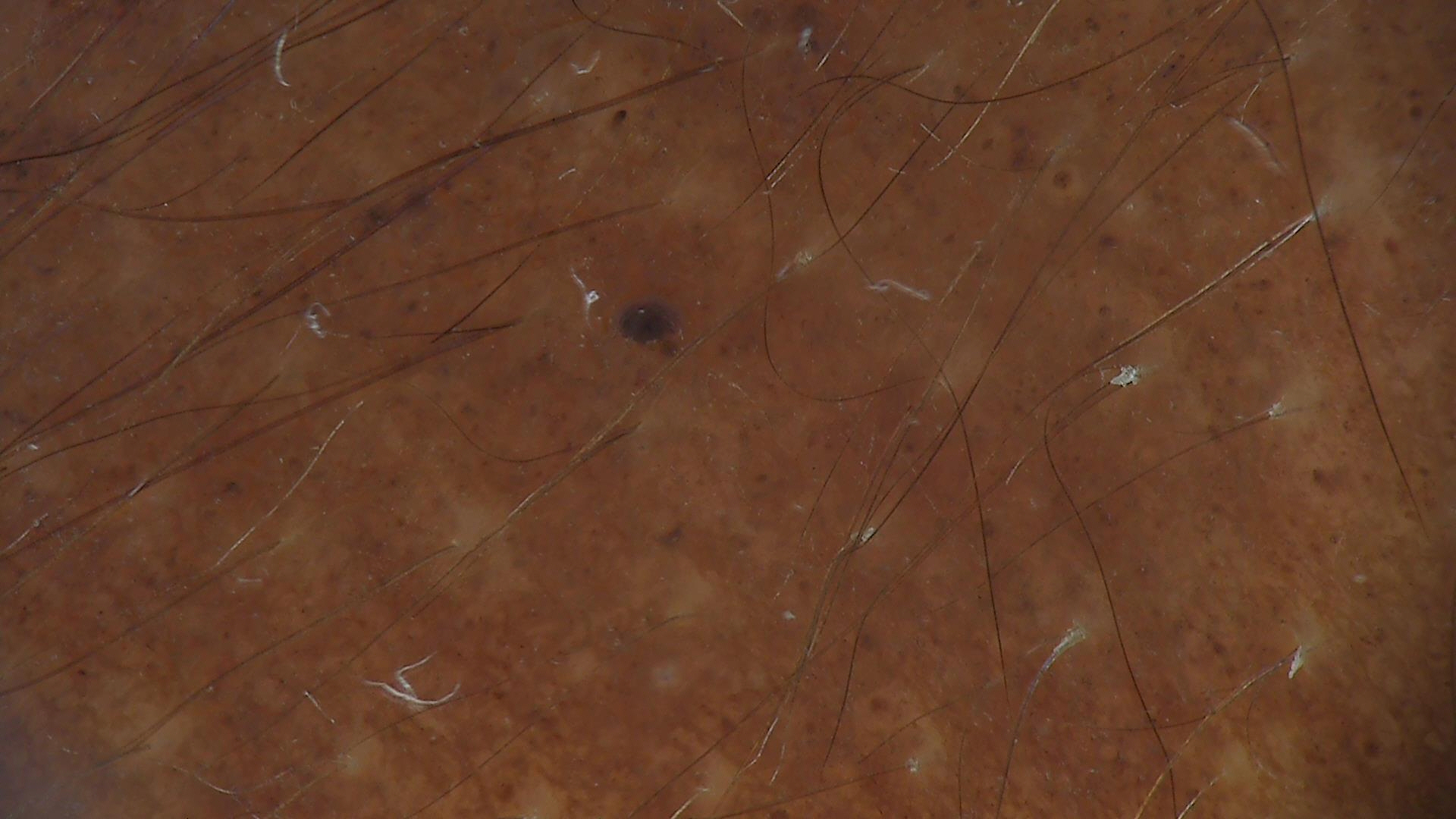assessment: congenital junctional nevus (expert consensus).